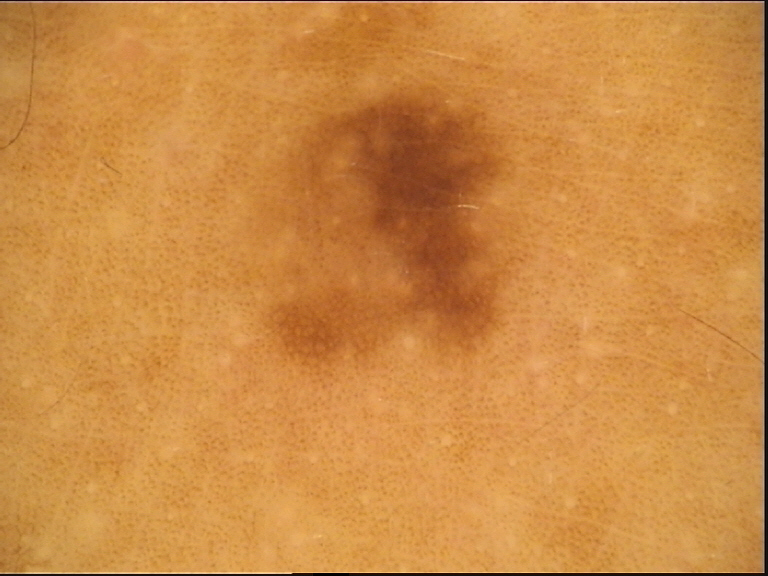A dermatoscopic image of a skin lesion. The diagnostic label was a dysplastic junctional nevus.